FST I; lay graders estimated Monk skin tone scale 1 or 2. Close-up view. Texture is reported as raised or bumpy. The patient is 50–59, female. The affected area is the front of the torso. The condition has been present for less than one week. The patient indicates itching:
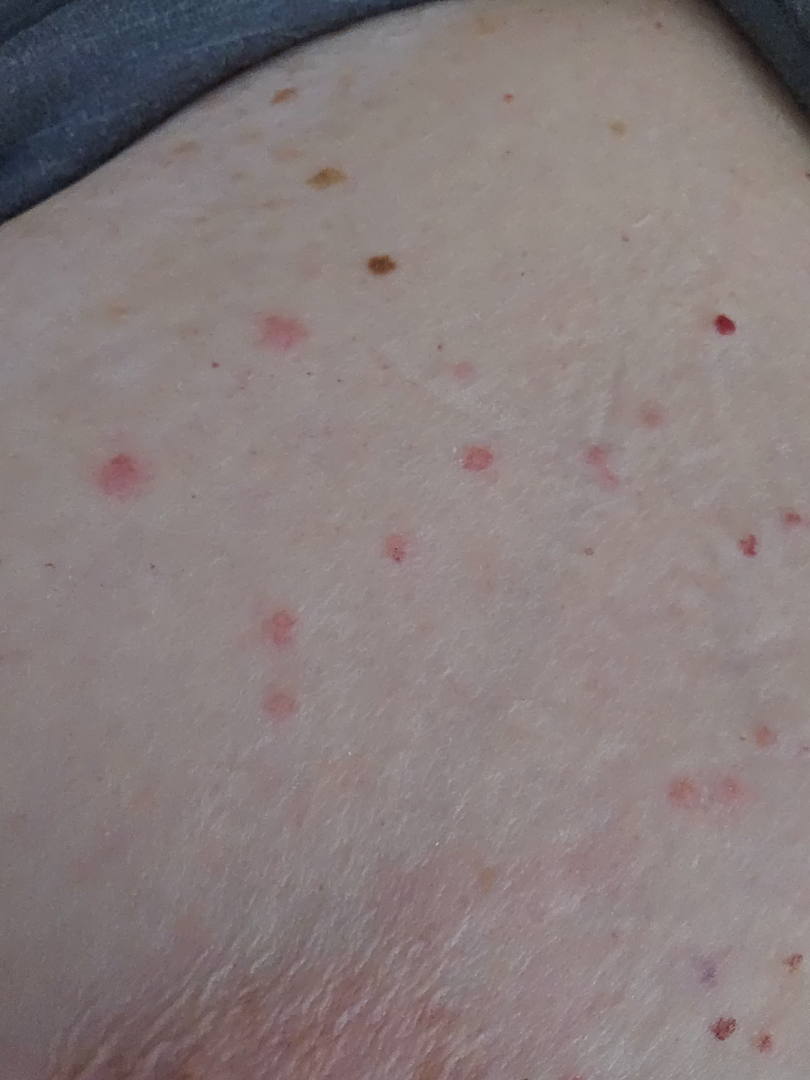Reviewed remotely by one dermatologist: the leading consideration is Psoriasis; the differential also includes Eczema; an alternative is Insect Bite.